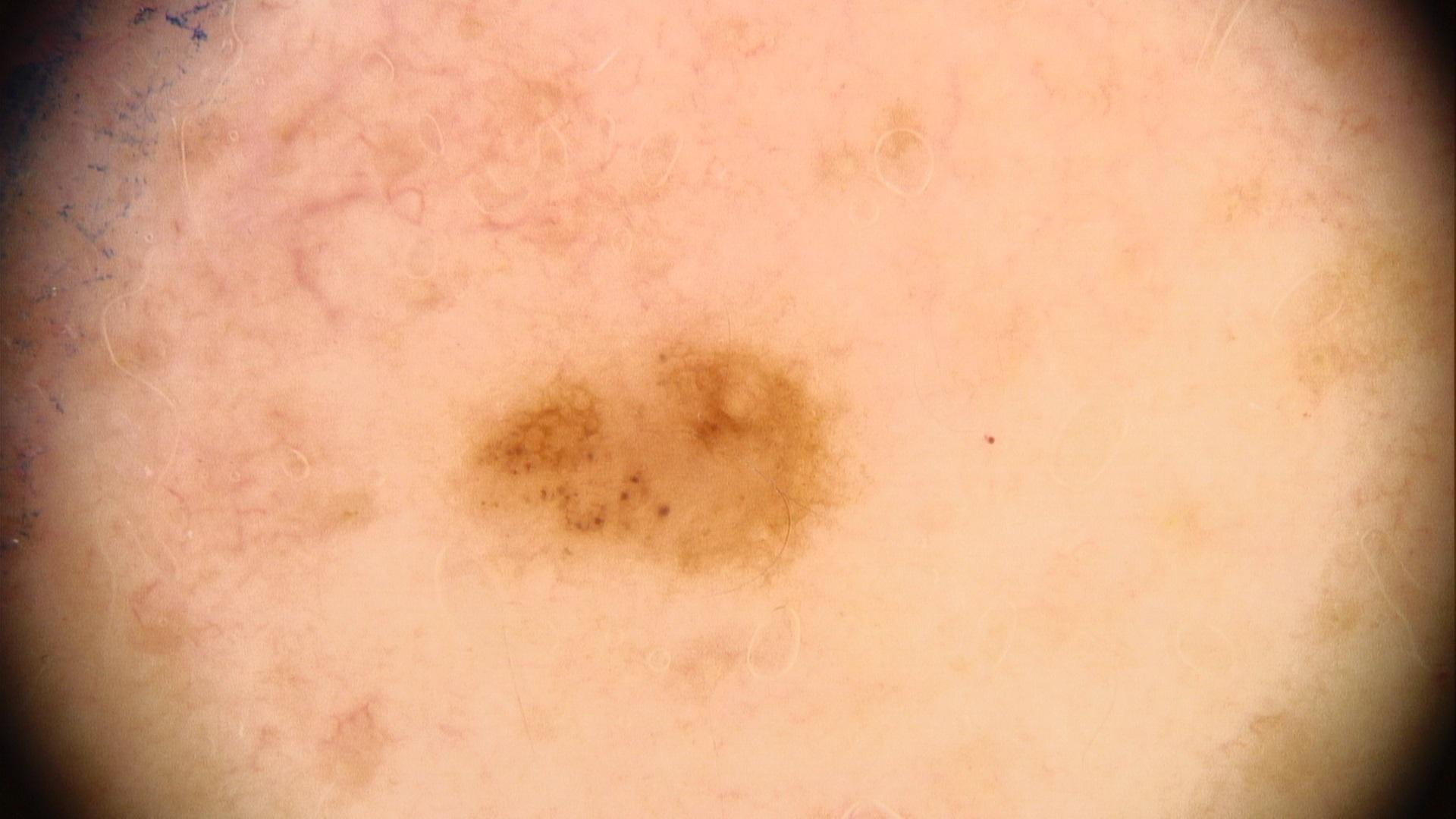Histopathology confirmed a nevus.